A smartphone photograph of a skin lesion. A subject age 53:
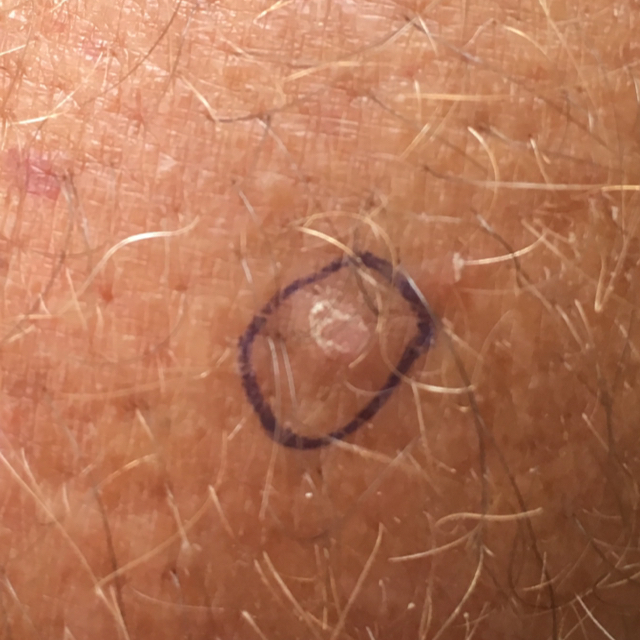Summary:
The lesion involves a forearm. By the patient's account, the lesion is elevated and itches, but has not changed and does not hurt.
Conclusion:
The consensus clinical diagnosis was a premalignant lesion — an actinic keratosis.